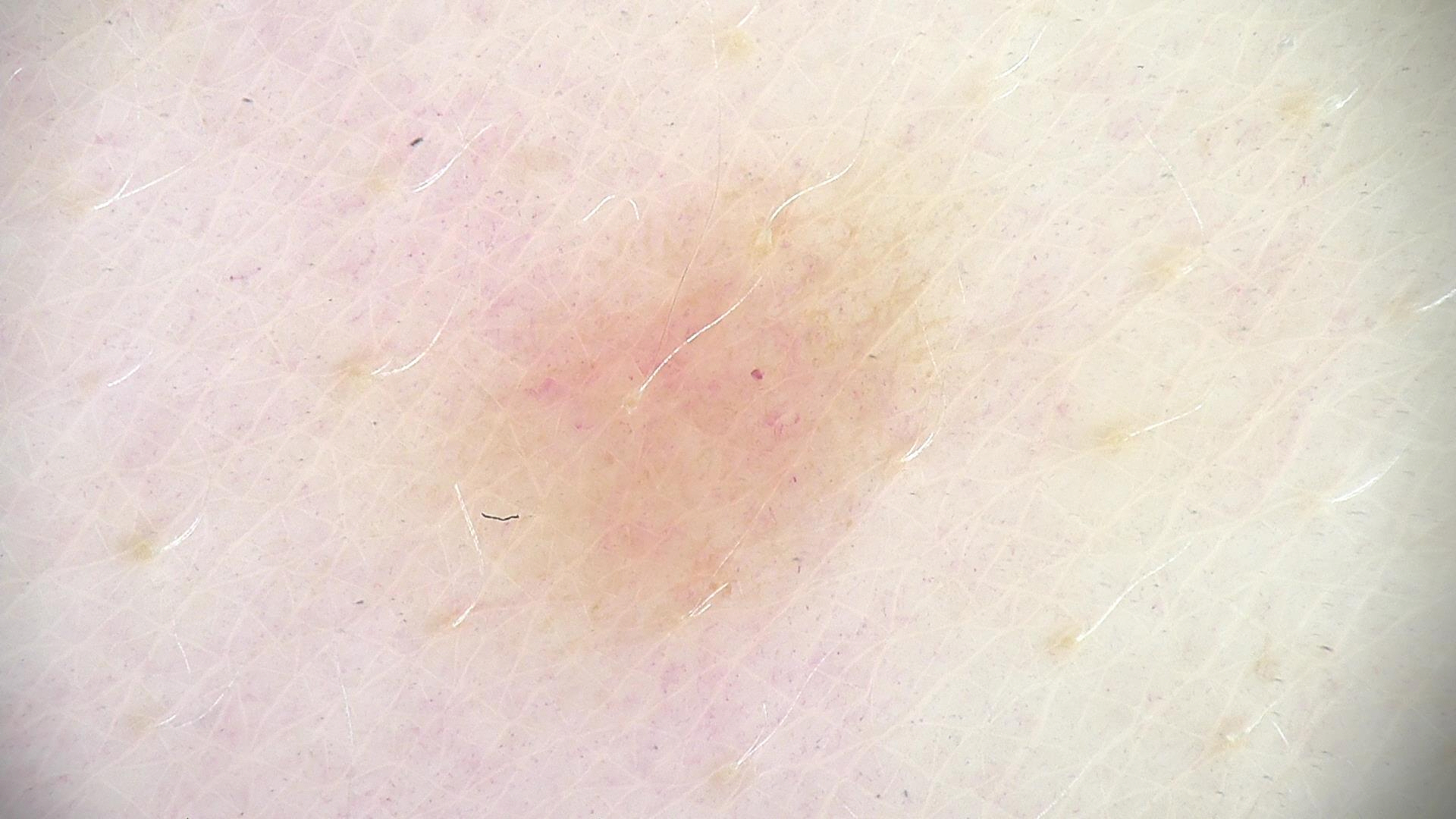Q: What is the diagnosis?
A: dysplastic junctional nevus (expert consensus)